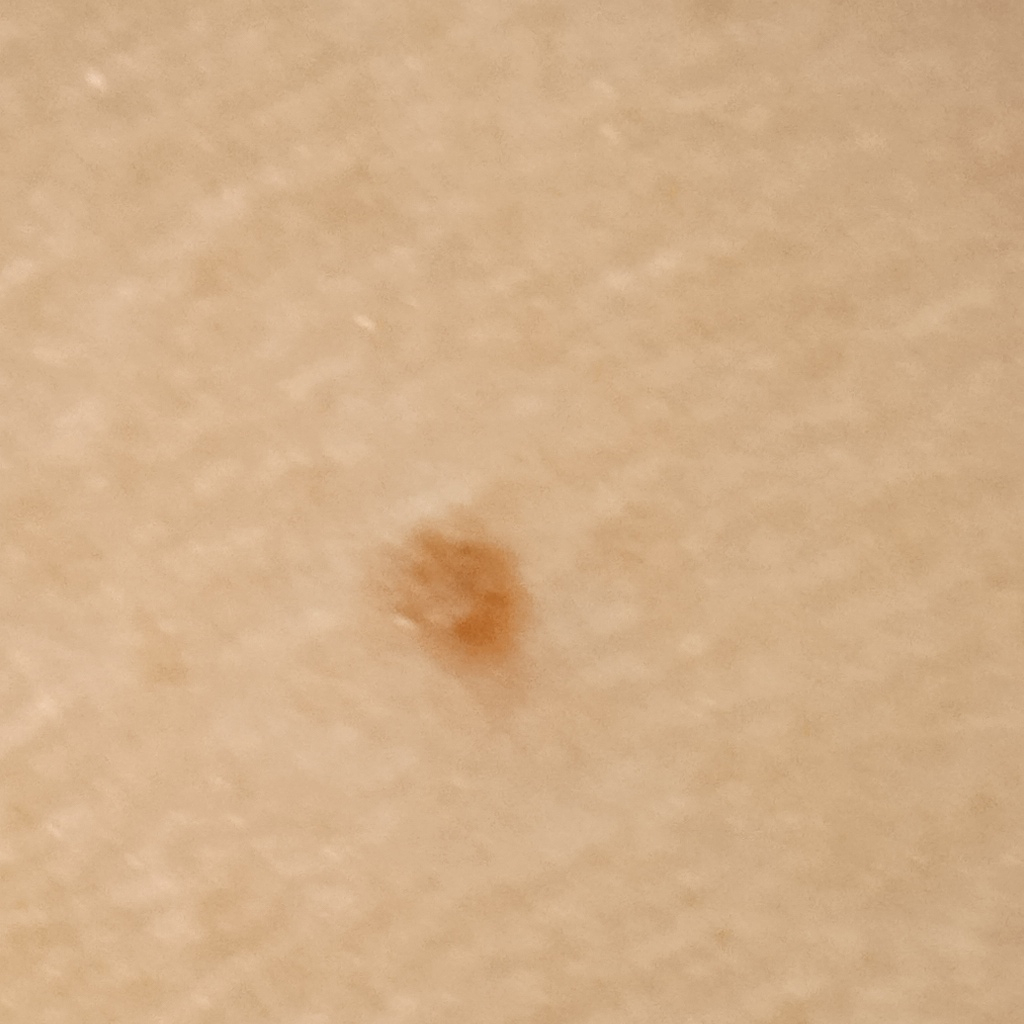Impression: The consensus diagnosis for this lesion was a melanocytic nevus.